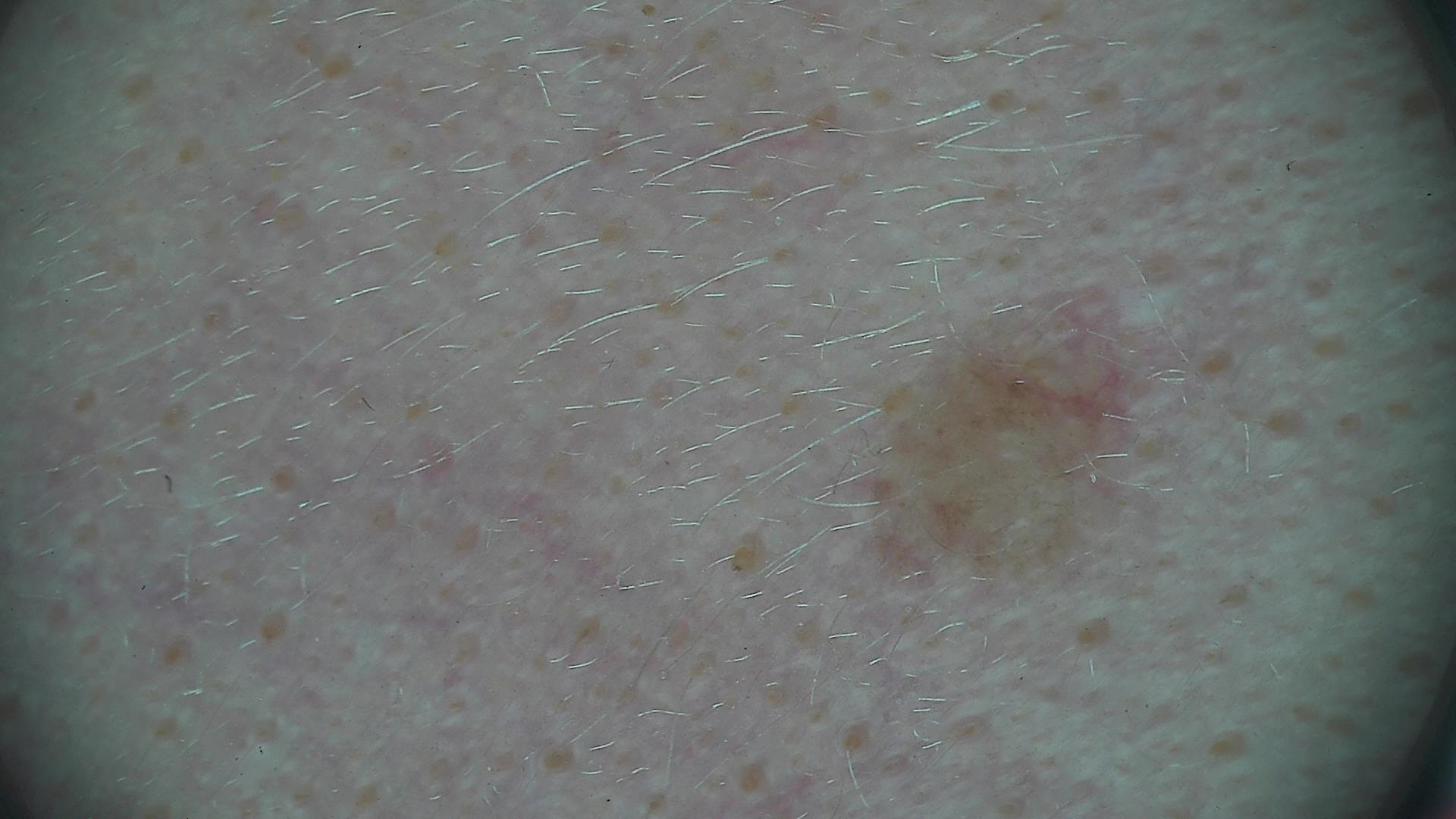Consistent with a dysplastic junctional nevus.